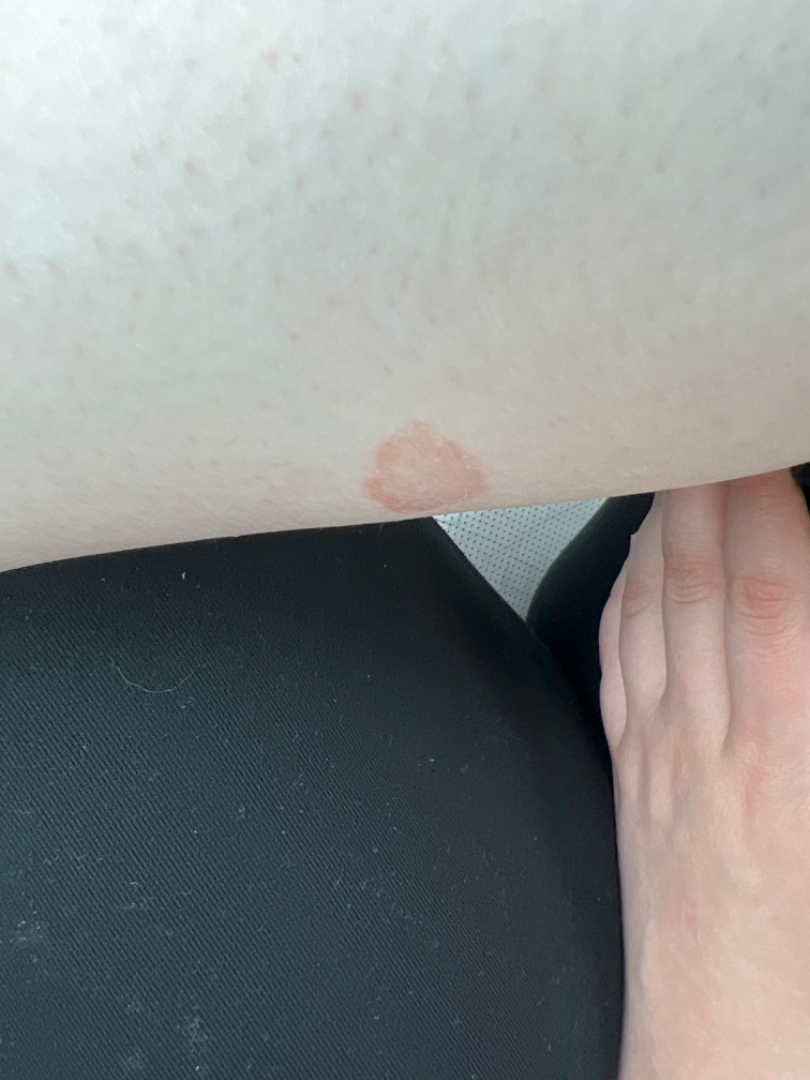Eczema (weight 0.35); Tinea (weight 0.33); Porokeratosis (weight 0.23); Granuloma annulare (weight 0.10).